The subject is a female roughly 80 years of age; a dermoscopic image of a skin lesion:
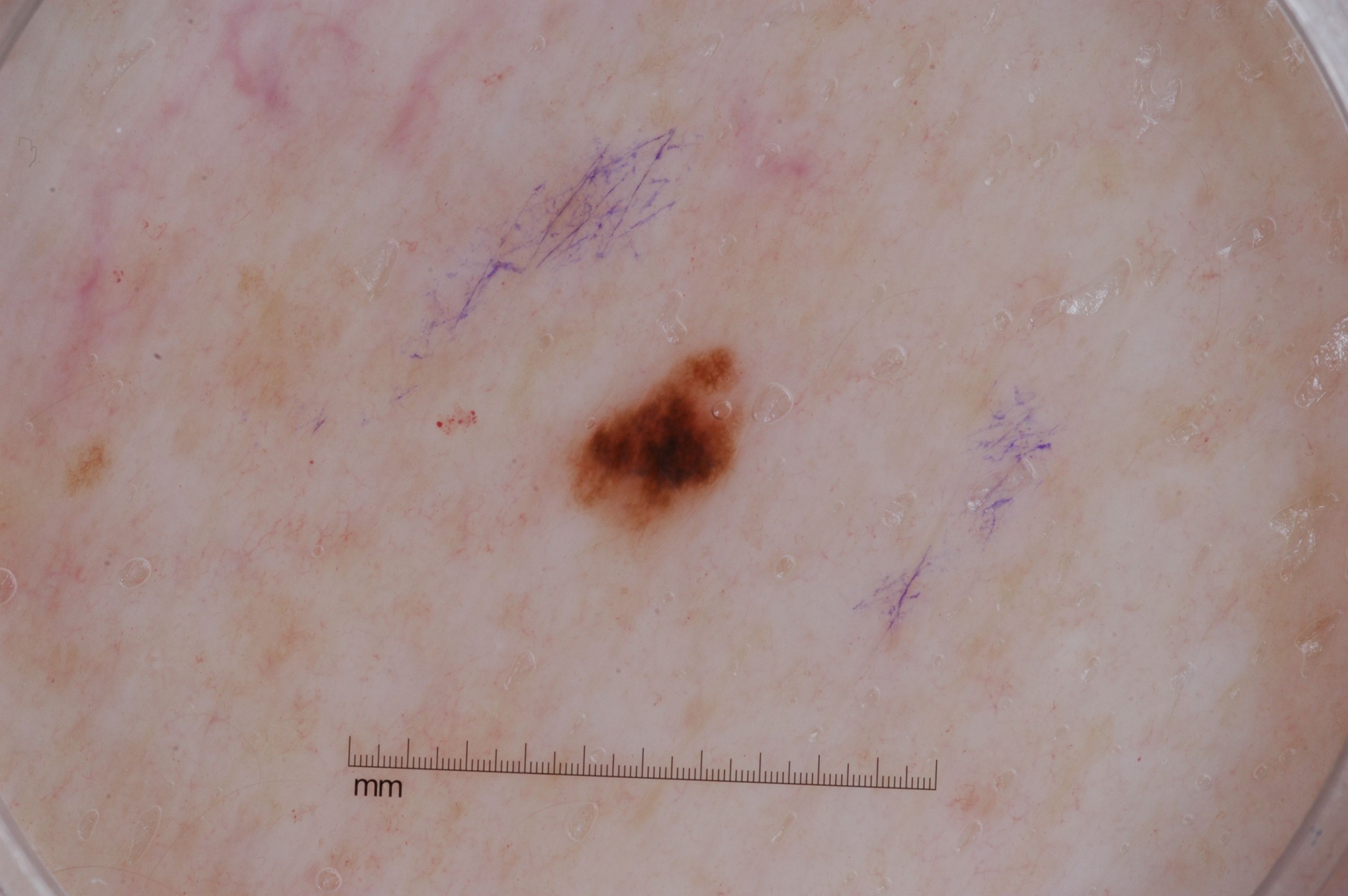The lesion occupies the region [569,357,747,539]. The dermoscopic pattern shows pigment network; no streaks, milia-like cysts, or negative network. Clinically diagnosed as a melanocytic nevus, a benign skin lesion.